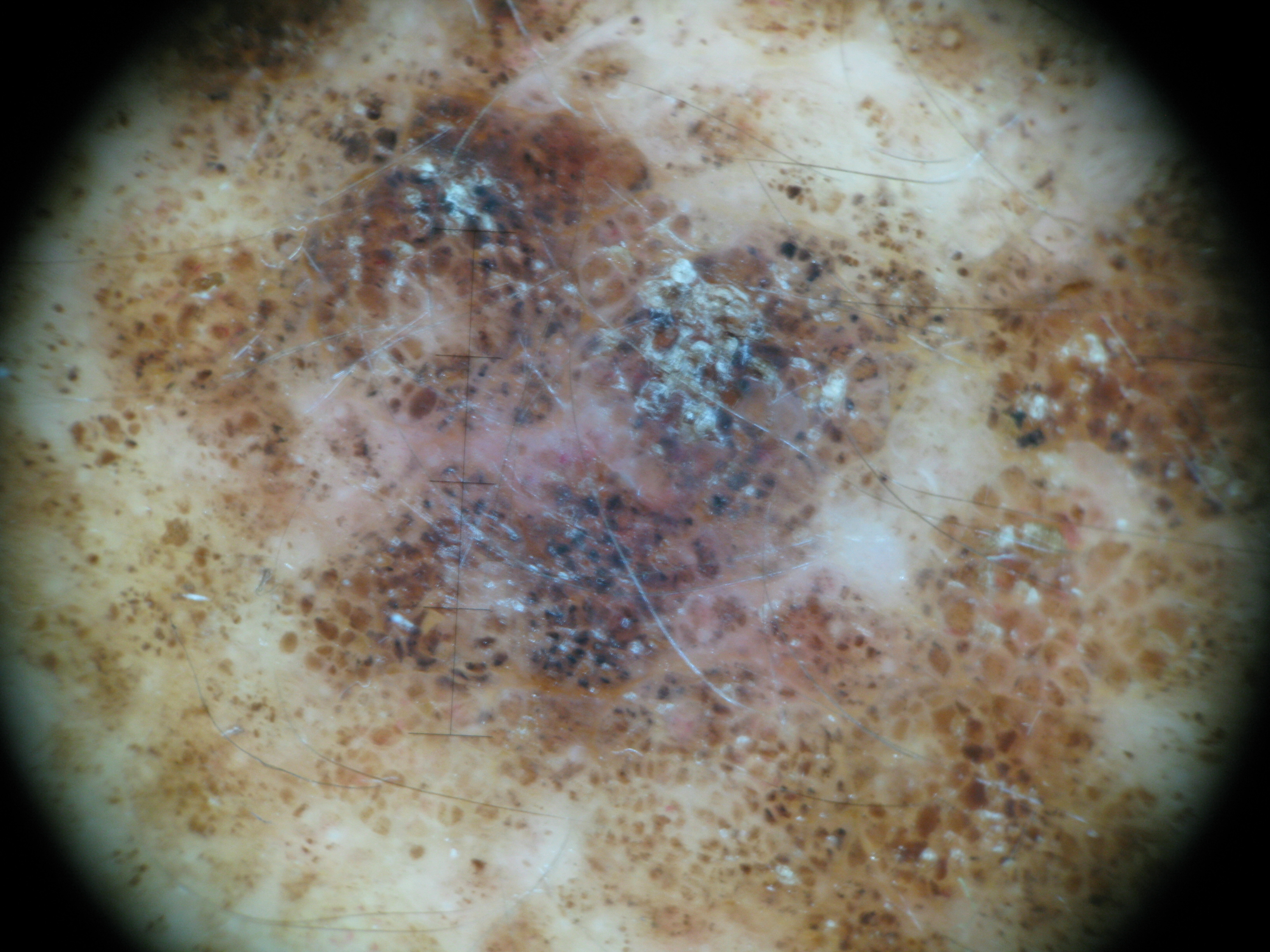A dermoscopic image of a skin lesion. Histopathologically confirmed as a melanoma.